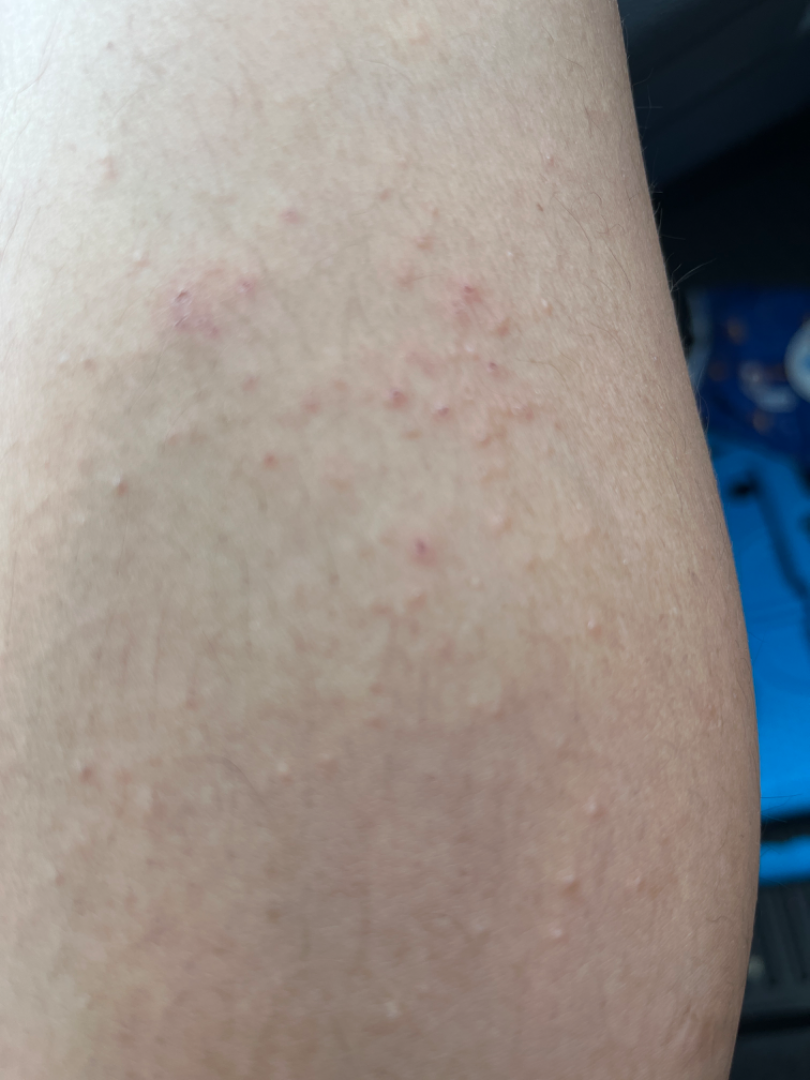Symptoms reported: itching and burning. The arm, head or neck and leg are involved. Present for about one day. The patient considered this a rash. The lesion is described as fluid-filled and raised or bumpy. A close-up photograph. On photographic review, Eczema (considered); Folliculitis (considered).